A skin lesion imaged with a dermatoscope:
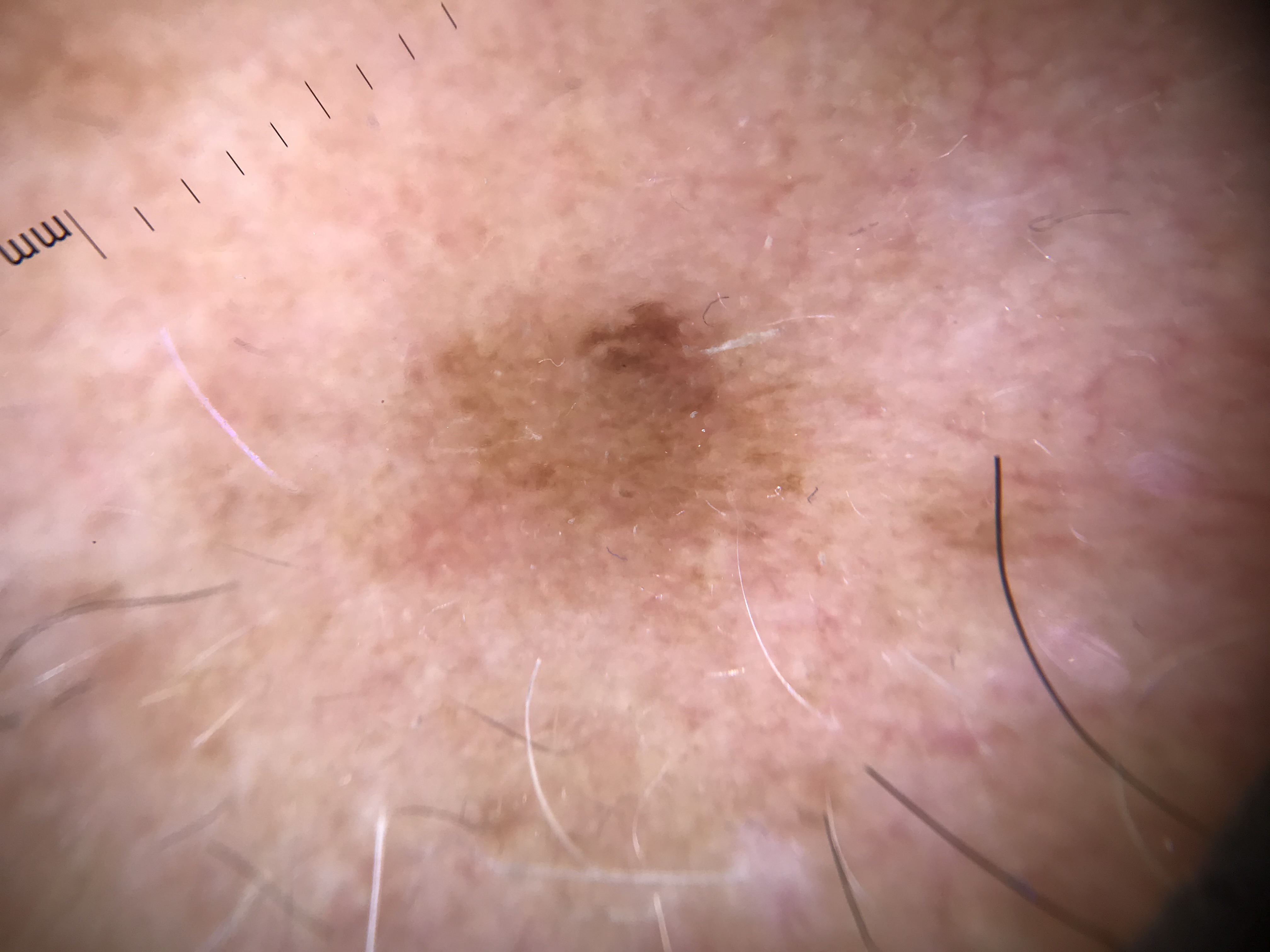assessment = seborrheic keratosis (expert consensus)